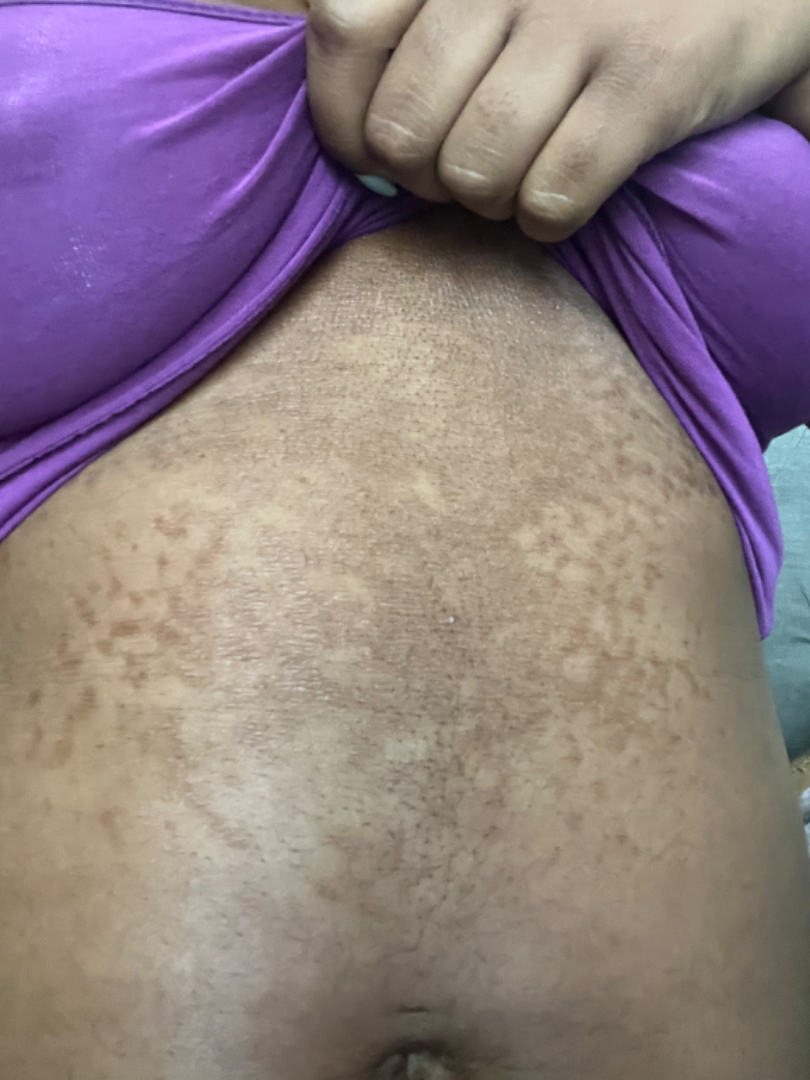On remote review of the image, the impression is Confluent and reticulate papillomatosis.